Dermoscopy of a skin lesion: 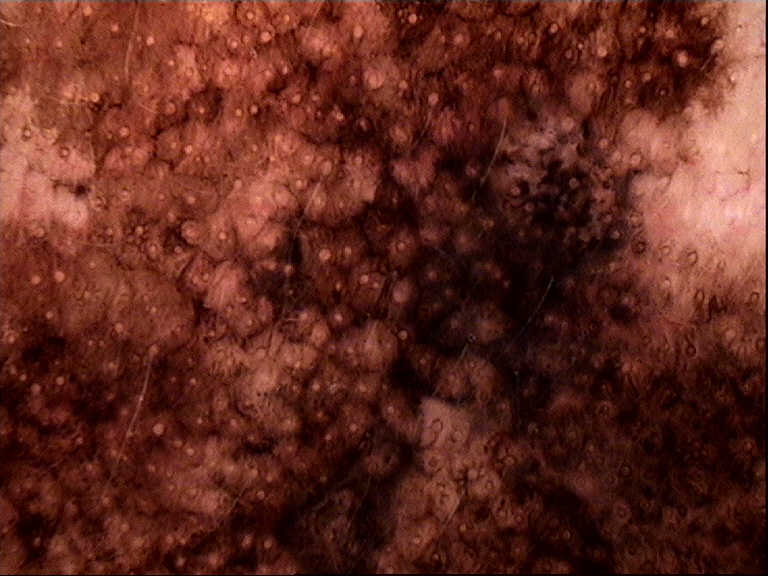Biopsy-confirmed as a lentigo maligna.